The chart records a previous melanoma.
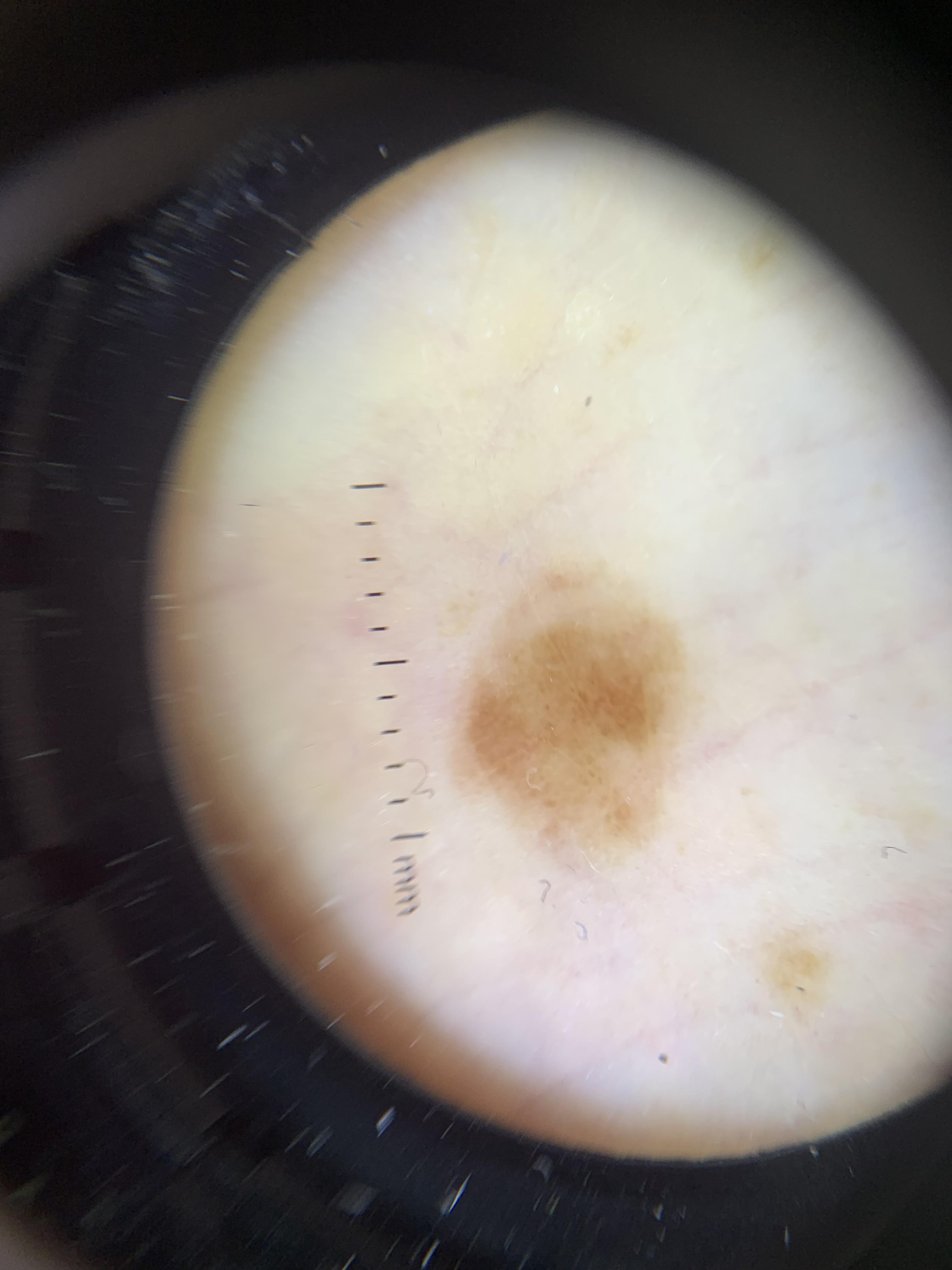The lesion involves a lower extremity.
Histopathology confirmed a lesion of melanocytic lineage — a nevus.